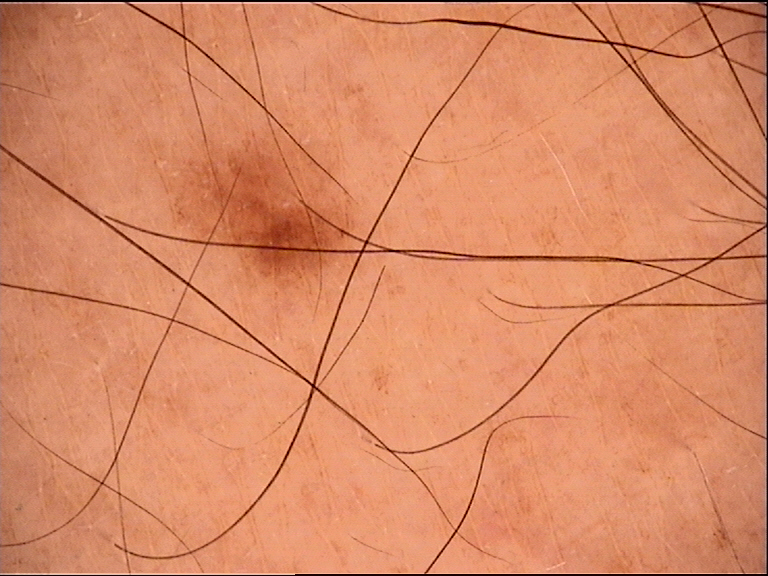diagnosis:
  name: dysplastic junctional nevus
  code: jd
  malignancy: benign
  super_class: melanocytic
  confirmation: expert consensus